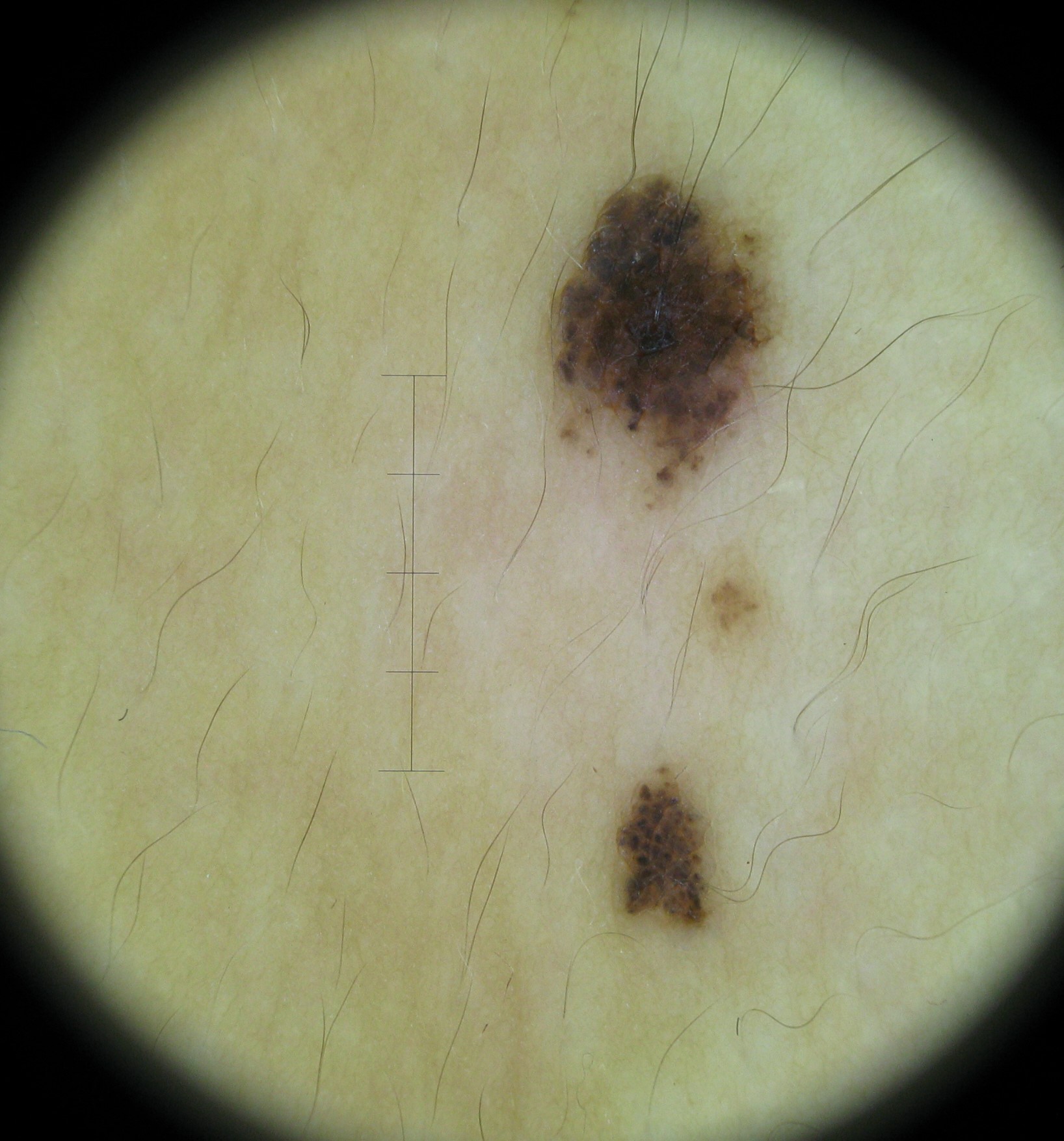The morphology is that of a banal lesion. Labeled as a compound nevus.